An image taken at an angle.
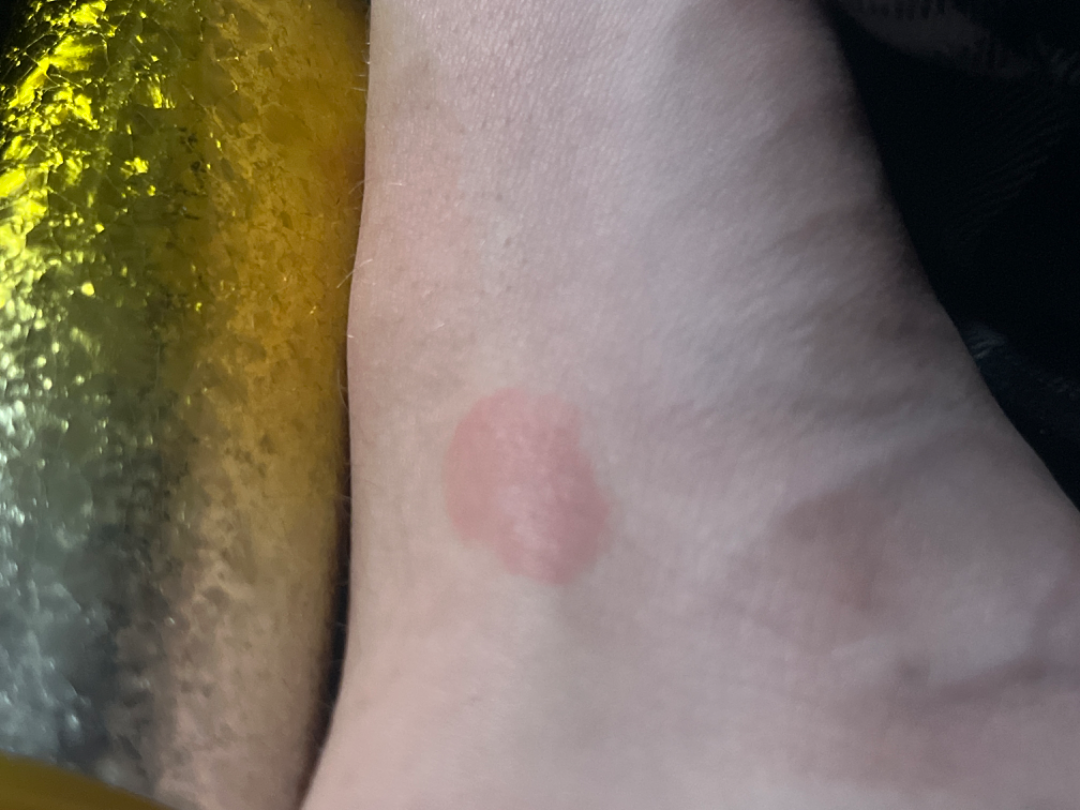The reviewing dermatologist's impression was: Tinea, Eczema and Allergic Contact Dermatitis were each considered, in no particular order.